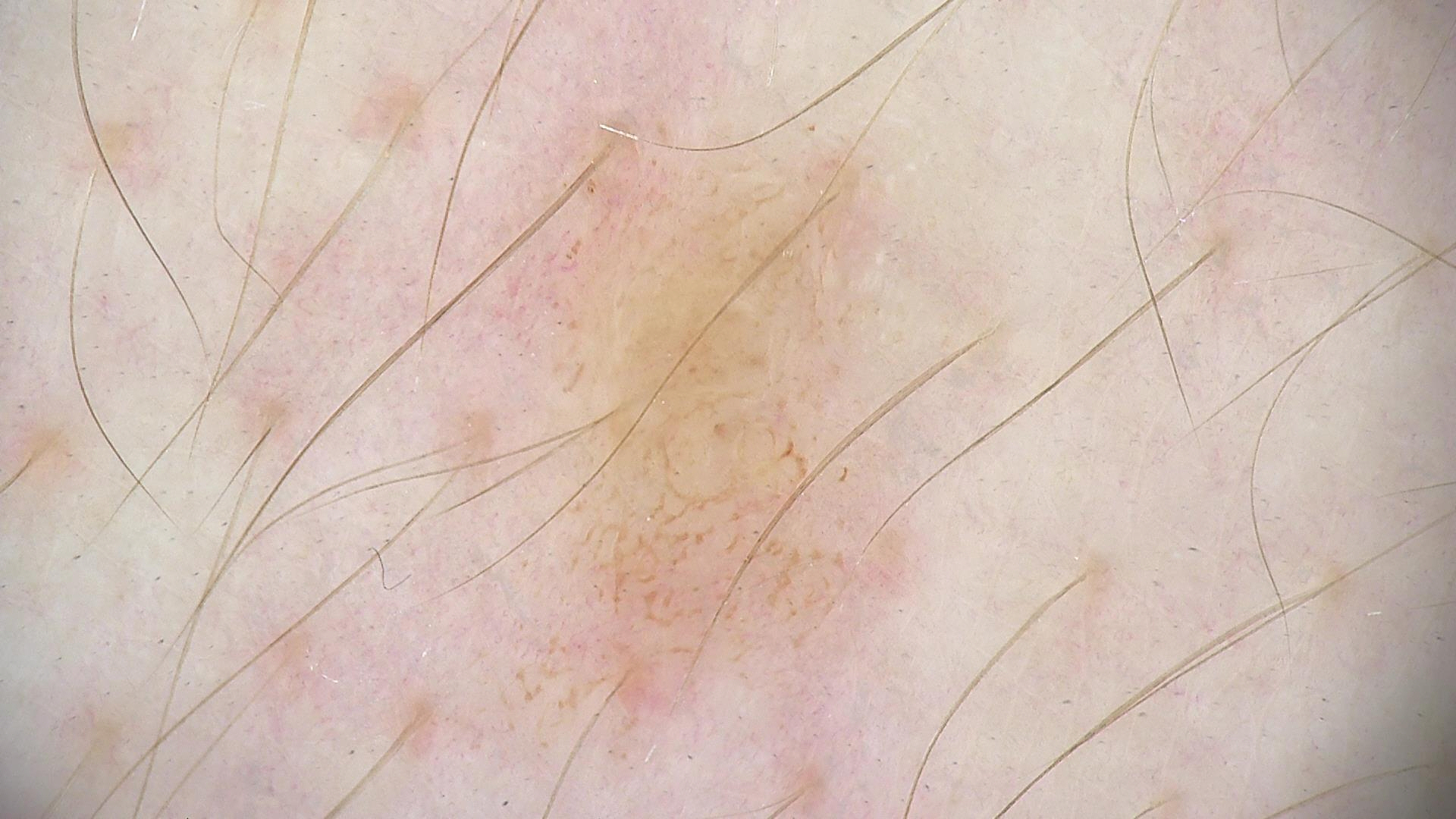image — dermatoscopy; label — dysplastic junctional nevus (expert consensus).